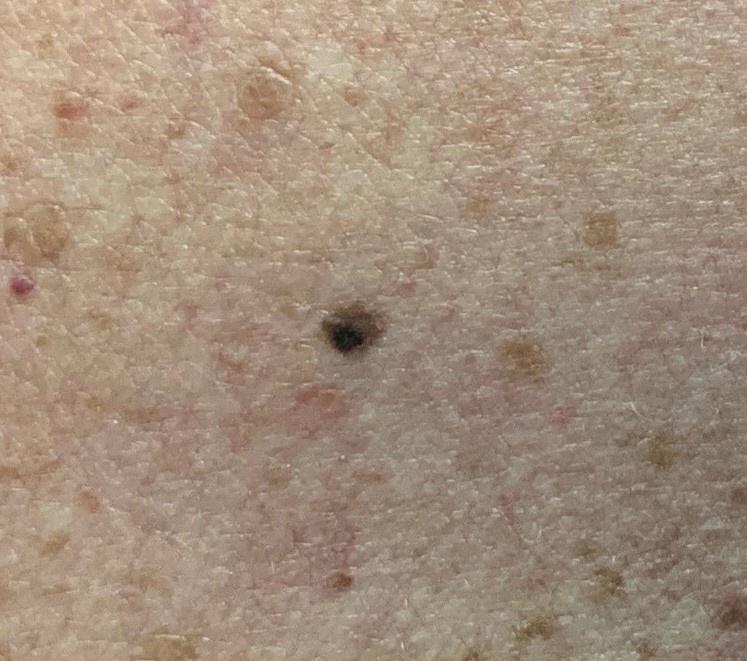A female subject roughly 75 years of age. Skin type II. The chart records a previous melanoma but no melanoma in first-degree relatives. An overview clinical photograph of a skin lesion. The lesion is located on the posterior trunk. The biopsy diagnosis was a nevus.